A skin lesion imaged with a dermatoscope: 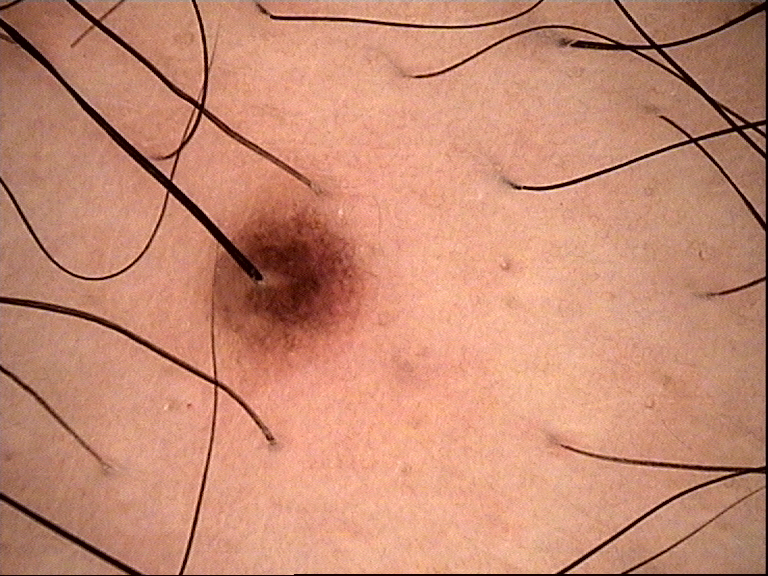Labeled as a compound nevus.